A male patient roughly 65 years of age · the patient is Fitzpatrick phototype II · a contact-polarized dermoscopy image of a skin lesion:
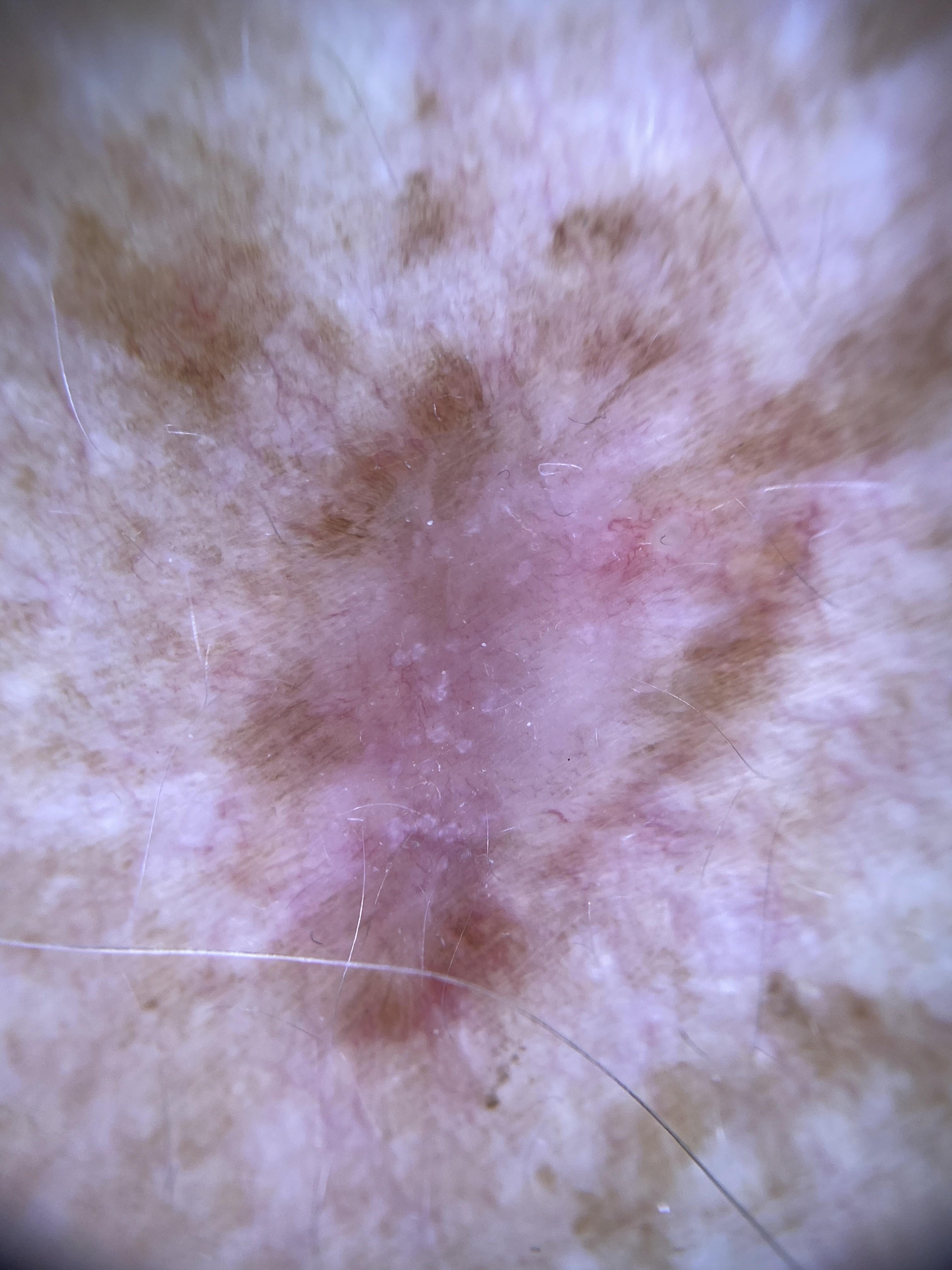diagnostic label — Basal cell carcinoma (biopsy-proven).